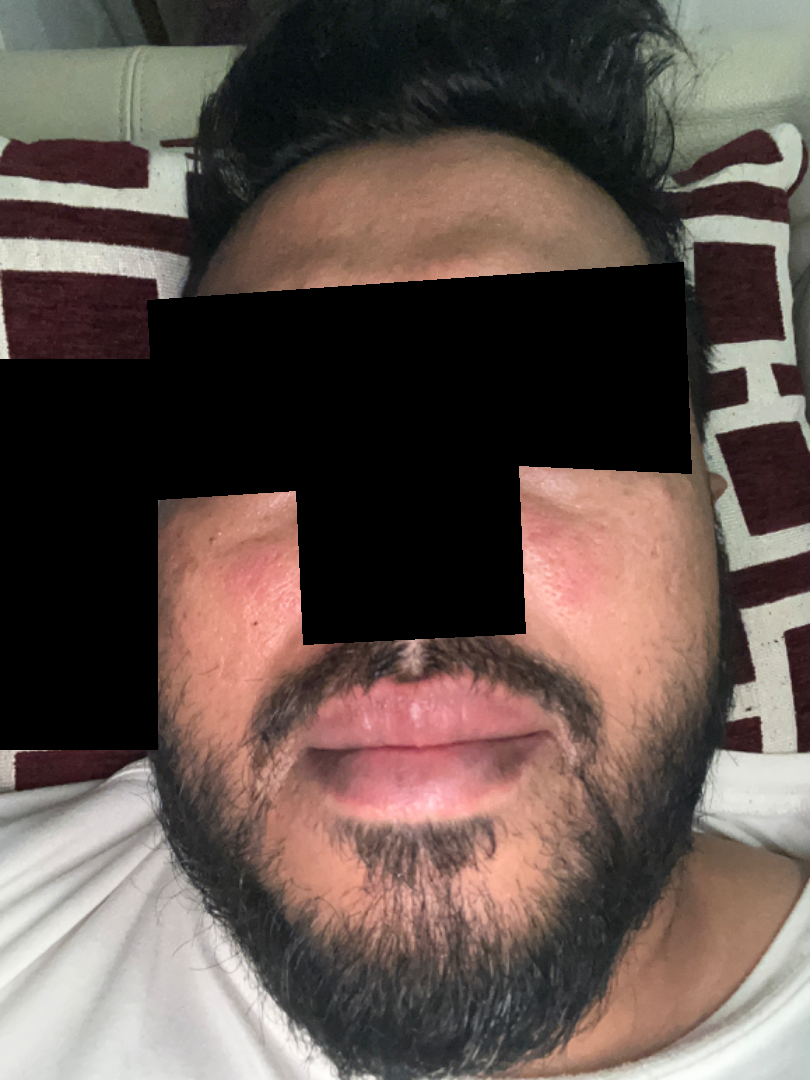  patient: male
  shot_type: close-up